A clinical photograph showing a skin lesion · a patient 67 years old: 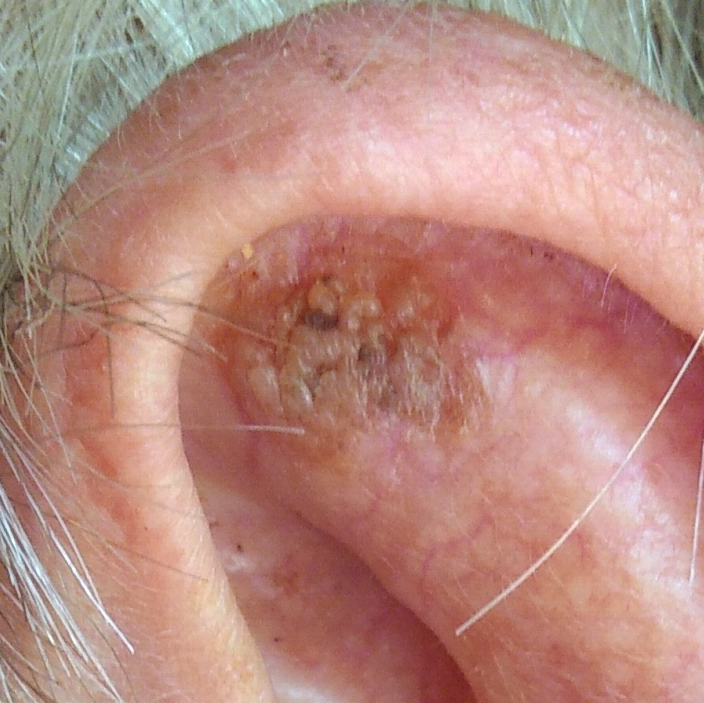The lesion was found on an ear. The patient reports that the lesion is elevated and itches, but has not grown and has not changed. Clinically diagnosed as a seborrheic keratosis.